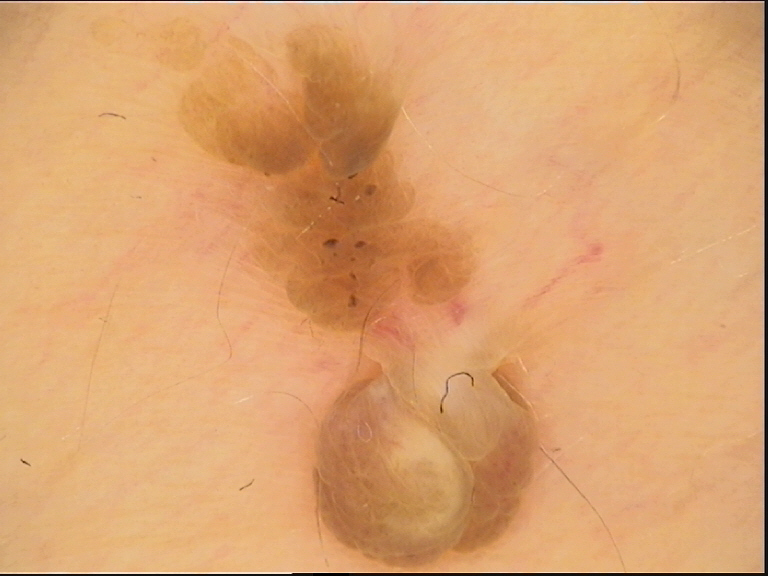Findings:
- label — seborrheic keratosis (expert consensus)